A dermoscopy image of a single skin lesion.
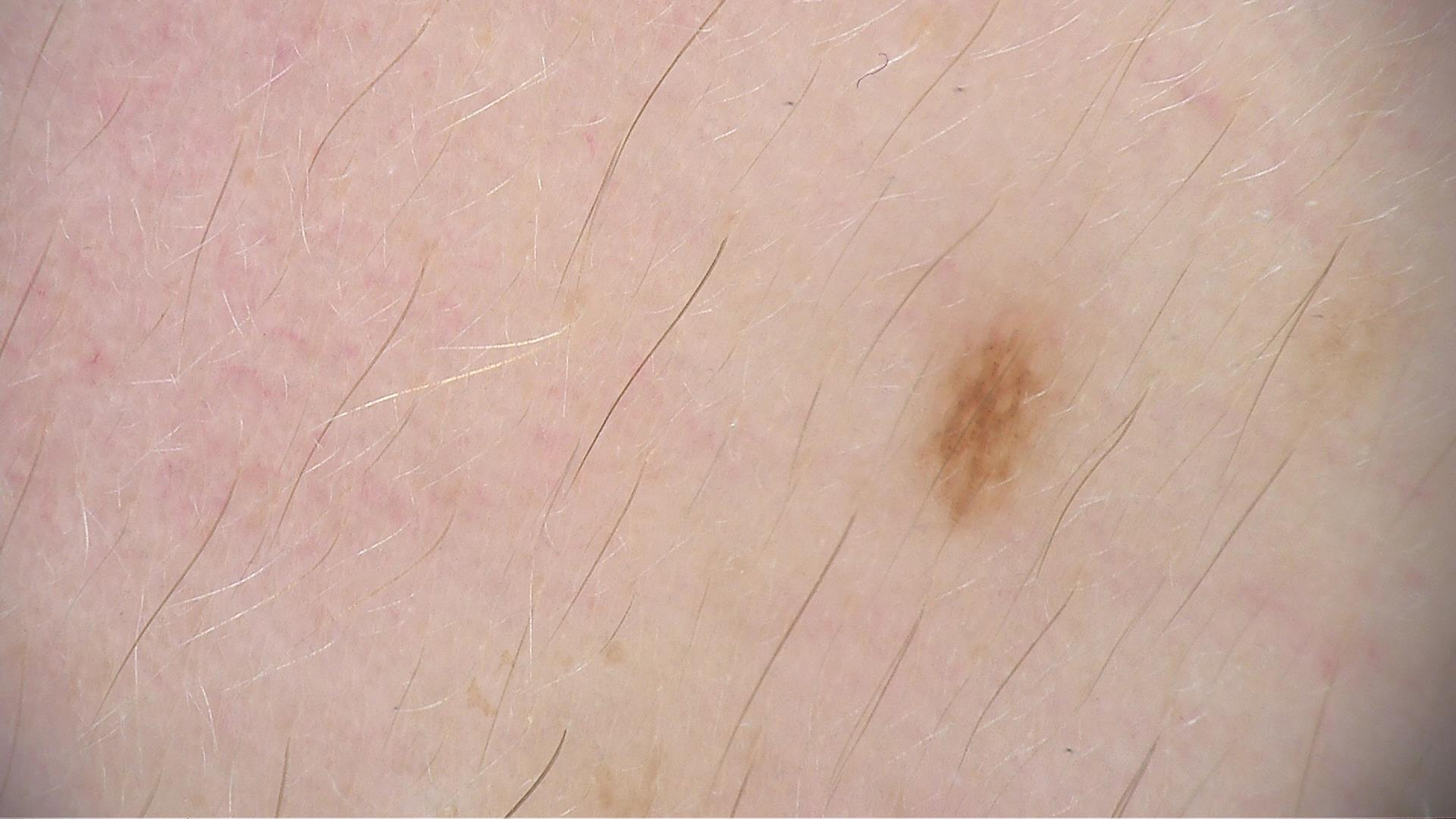Case: This is a banal lesion. Impression: Diagnosed as a junctional nevus.